A female subject 49 years old. The chart notes pesticide exposure, prior skin cancer (patient or family), no tobacco use, and no alcohol use. A clinical photograph of a skin lesion: 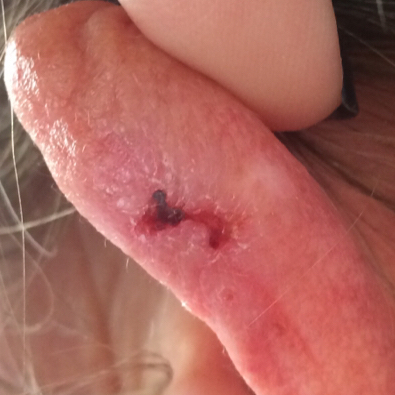<skin_lesion>
<lesion_location>an ear</lesion_location>
<symptoms>
<present>bleeding, pain, itching</present>
</symptoms>
<diagnosis>
<name>basal cell carcinoma</name>
<code>BCC</code>
<malignancy>malignant</malignancy>
<confirmation>histopathology</confirmation>
</diagnosis>
</skin_lesion>